A male patient, aged 38-42. A dermatoscopic image of a skin lesion — 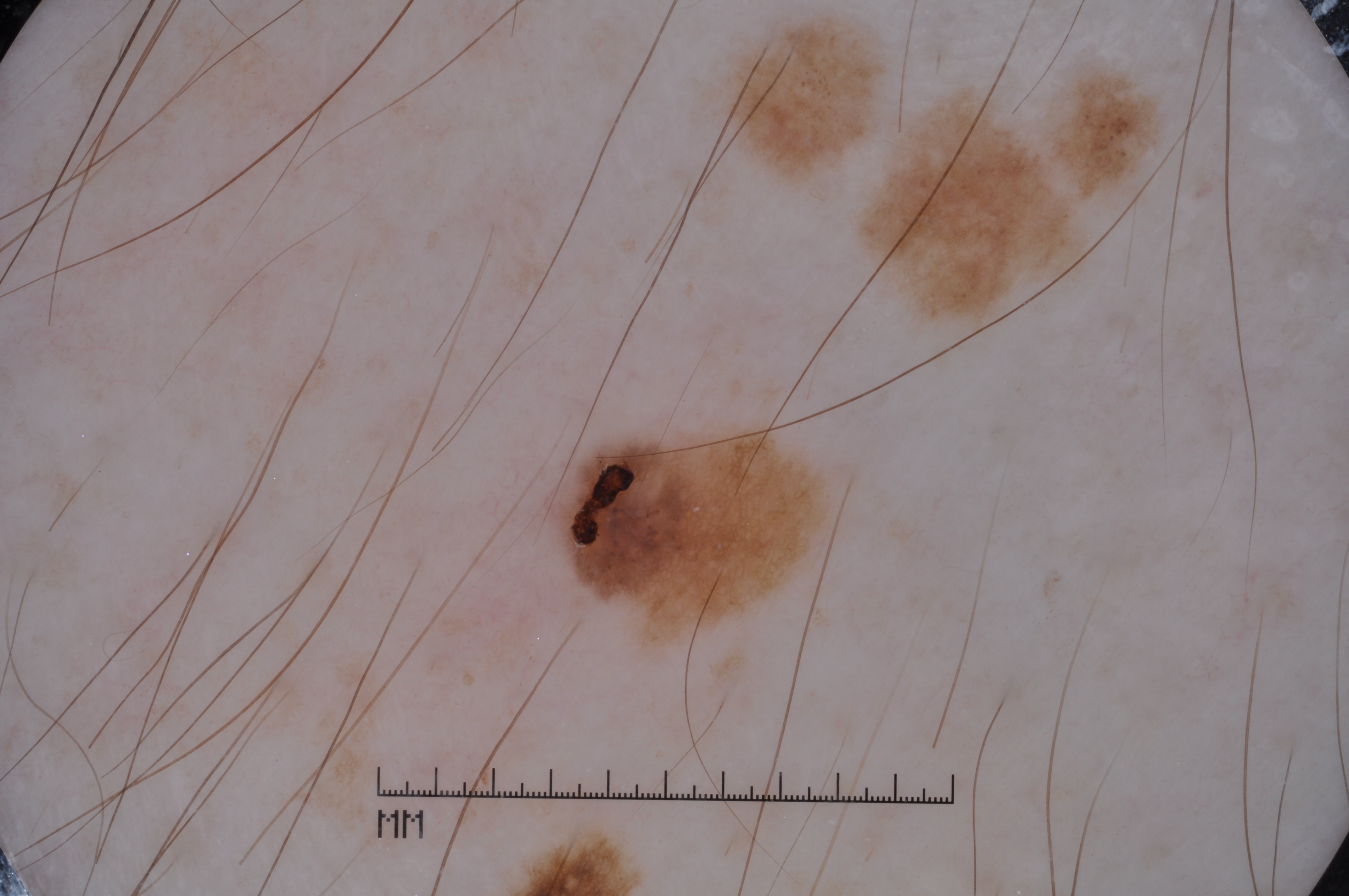  lesion_location:
    bbox_xyxy:
      - 554
      - 414
      - 834
      - 663
  lesion_extent: small
  dermoscopic_features:
    present:
      - pigment network
      - milia-like cysts
    absent:
      - streaks
      - negative network
  diagnosis:
    name: melanocytic nevus
    malignancy: benign
    lineage: melanocytic
    provenance: clinical